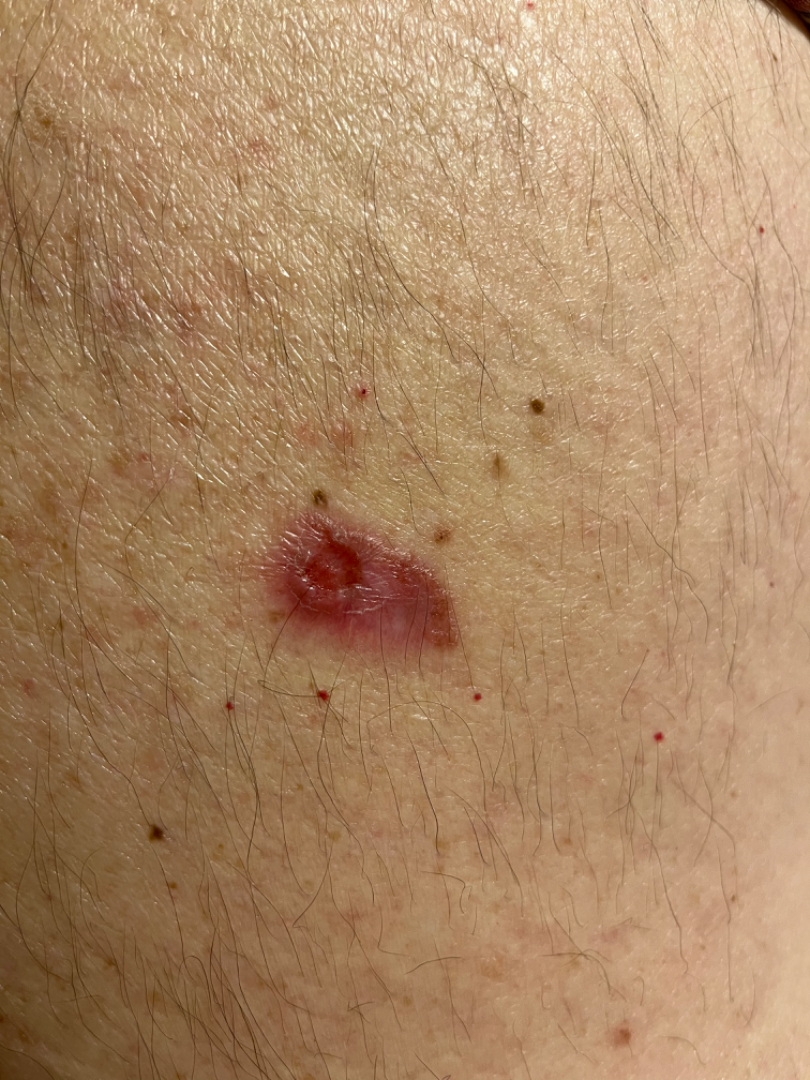Case summary:
- patient — male
- view — close-up
- body site — back of the torso
- diagnostic considerations — Basal Cell Carcinoma (leading); Inflicted skin lesions (considered); SCC/SCCIS (lower probability)